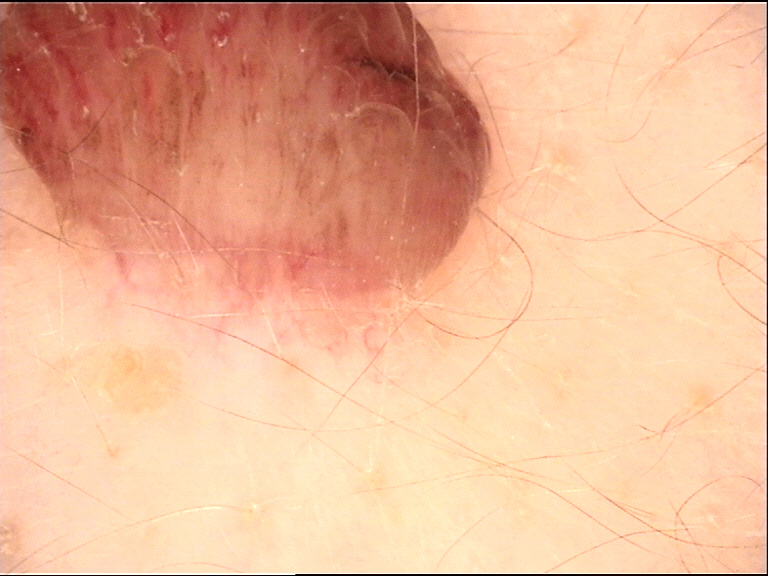modality: dermatoscopy; category: banal; label: dermal nevus (expert consensus).